The subject is male, the photo was captured at an angle, located on the arm: 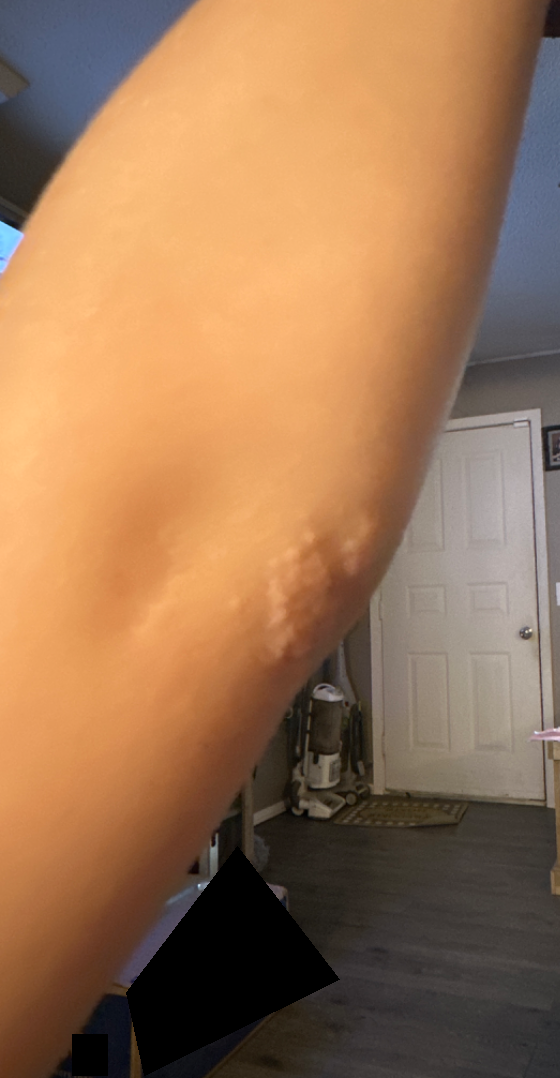A single dermatologist reviewed the case: Epidermal nevus, Verruca vulgaris and Psoriasis were each considered, in no particular order.